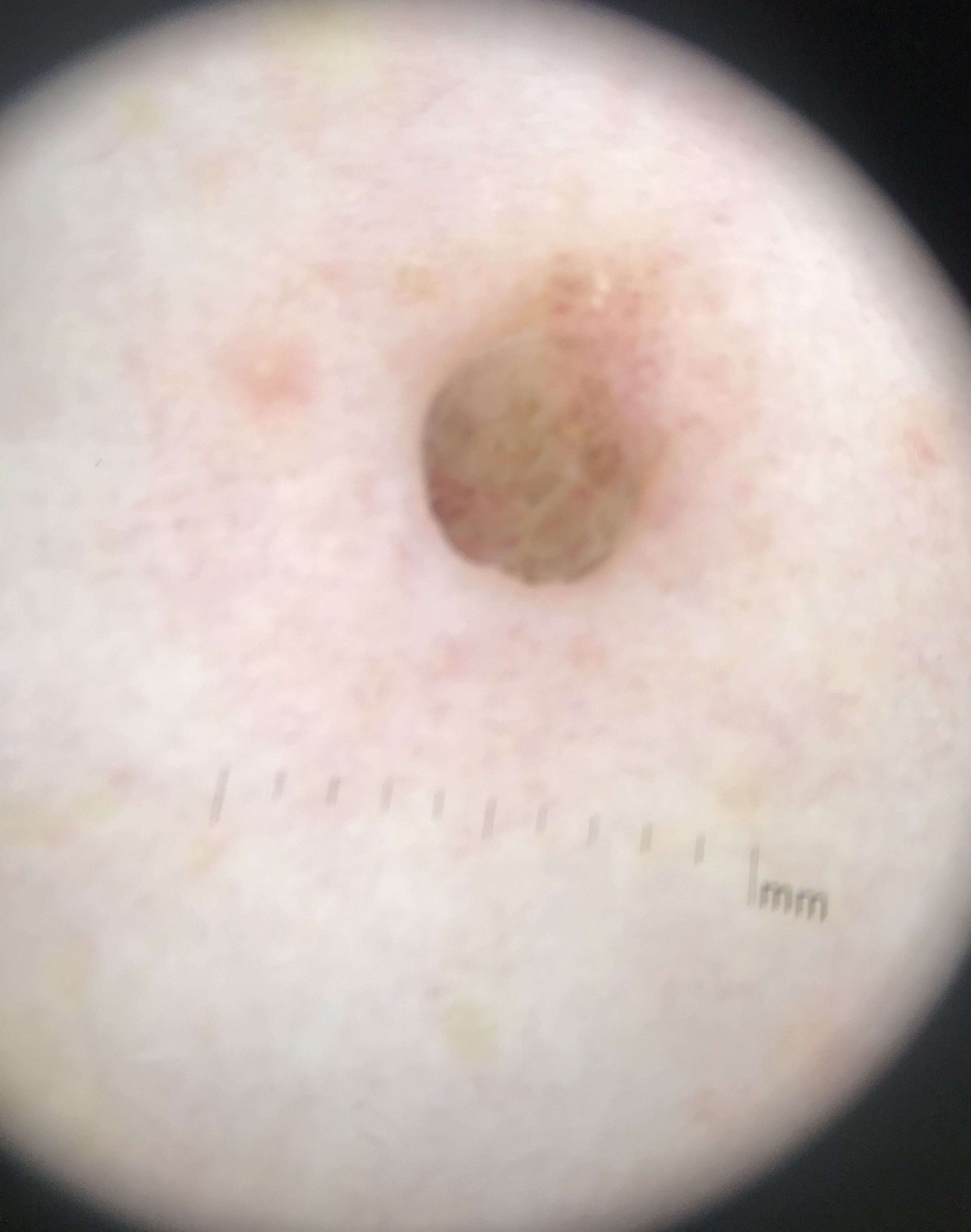lesion type=banal
label=dermal nevus (expert consensus)